The lesion involves the arm. The contributor is a female aged 30–39. Close-up view:
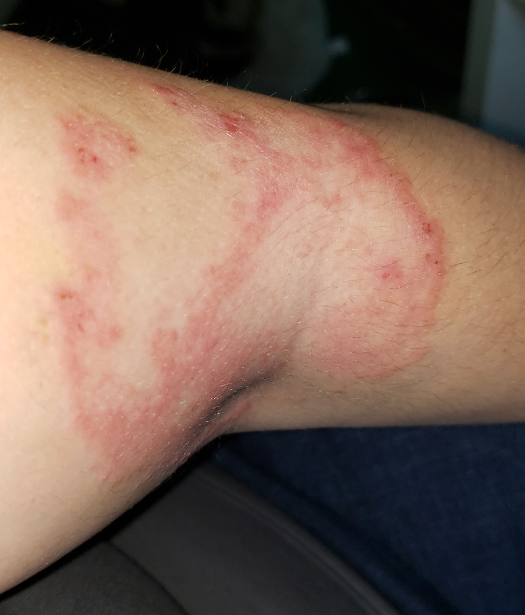Assessment:
Three dermatologists independently reviewed the case: the leading consideration is Tinea; less likely is Annular erythema; less probable is Eczema; lower on the differential is Erythema annulare centrifugum; a remote consideration is Erythema gyratum repens.